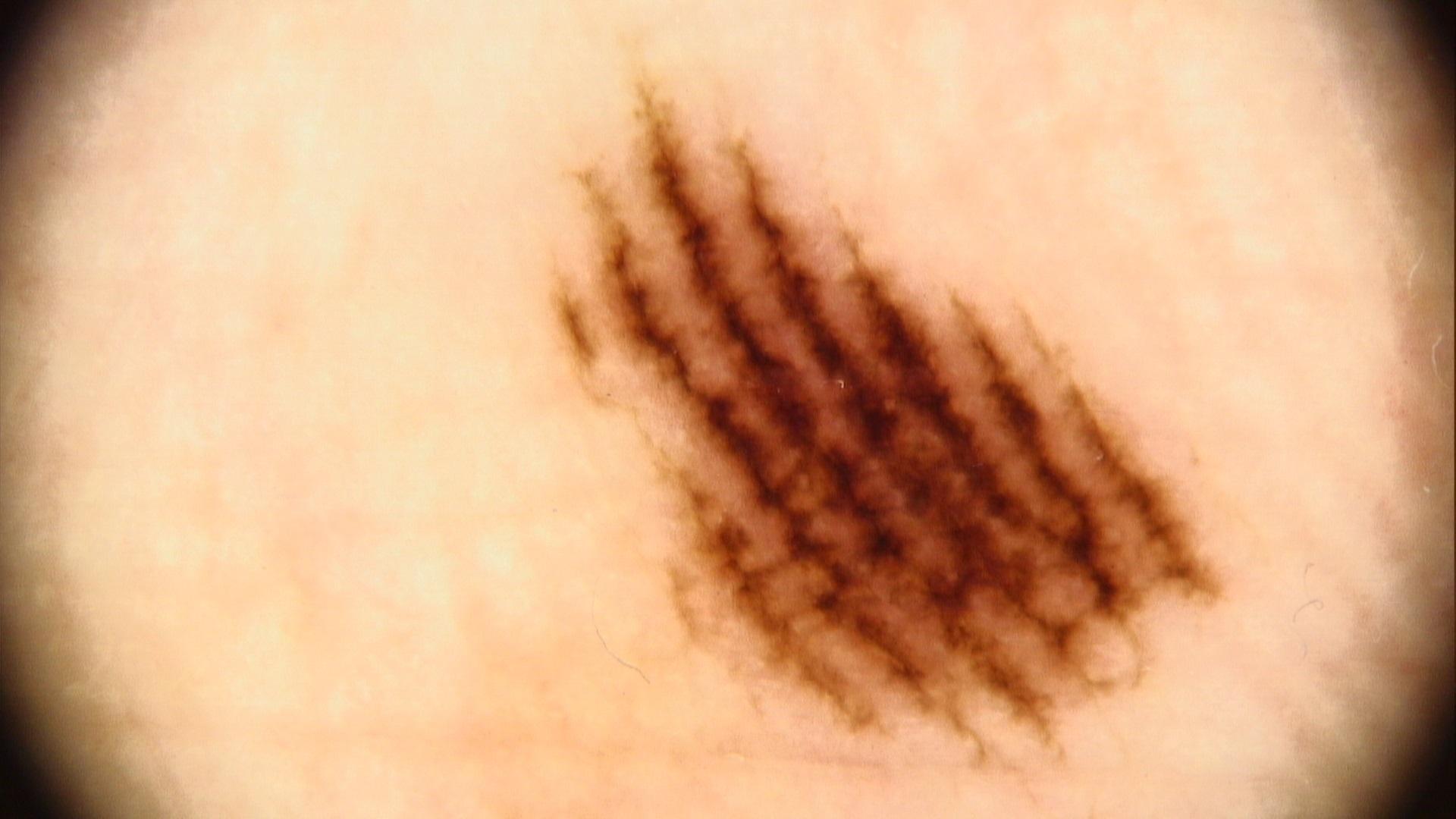Q: What kind of image is this?
A: contact-polarized dermoscopy
Q: Skin phototype?
A: III
Q: Who is the patient?
A: male, about 60 years old
Q: Where on the body is the lesion?
A: an acral site (palms or soles)
Q: What is the diagnosis?
A: Nevus